A male subject aged around 80 · the patient was assessed as Fitzpatrick II · a skin lesion imaged with a dermatoscope:
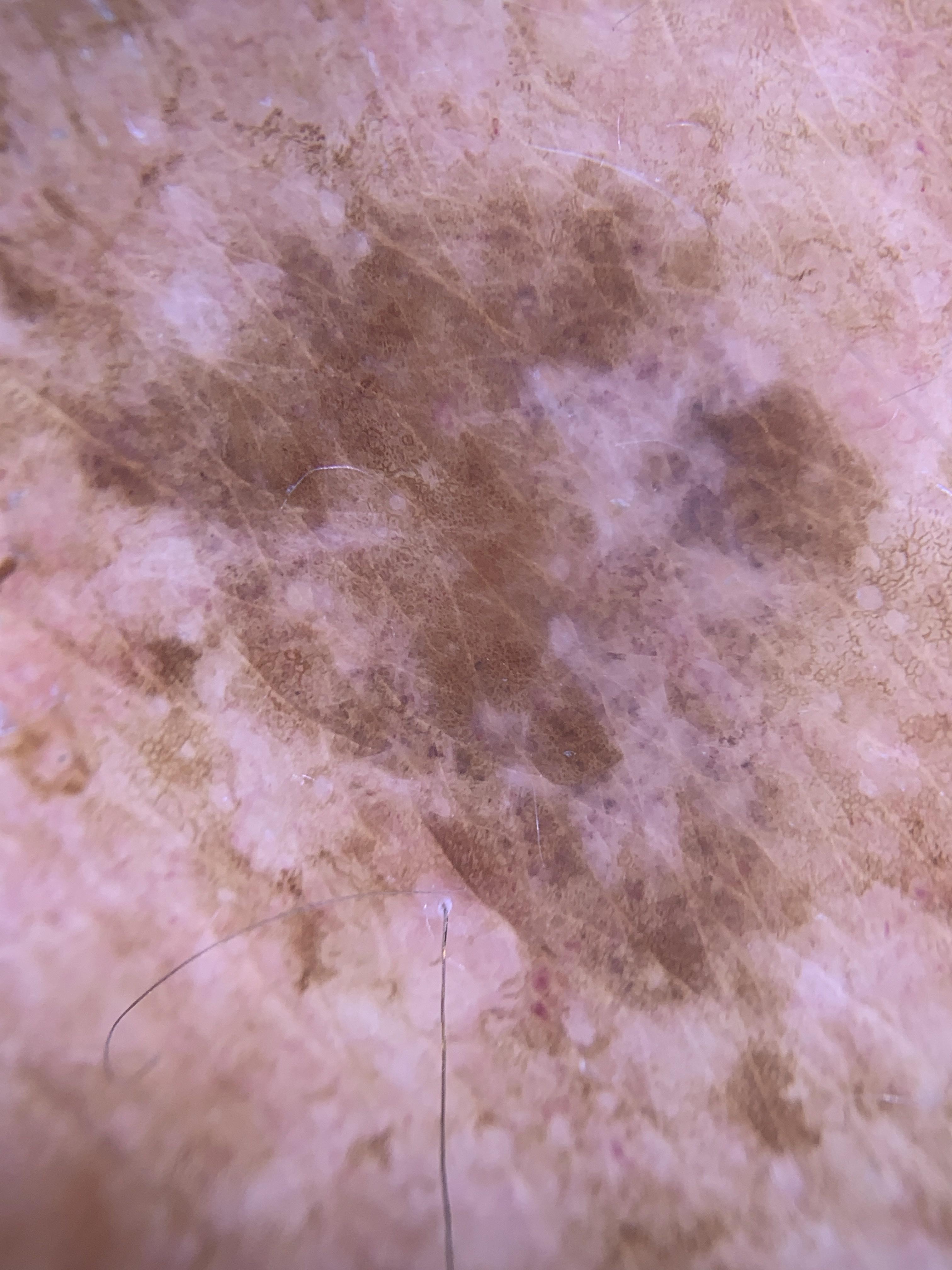Expert review favored a lichen planus like keratosis.